The leg is involved. The contributor notes the lesion is raised or bumpy. Skin tone: Fitzpatrick phototype II. The patient described the issue as acne. Symptoms reported: bothersome appearance. The photo was captured at a distance. The contributor notes the condition has been present for three to twelve months.
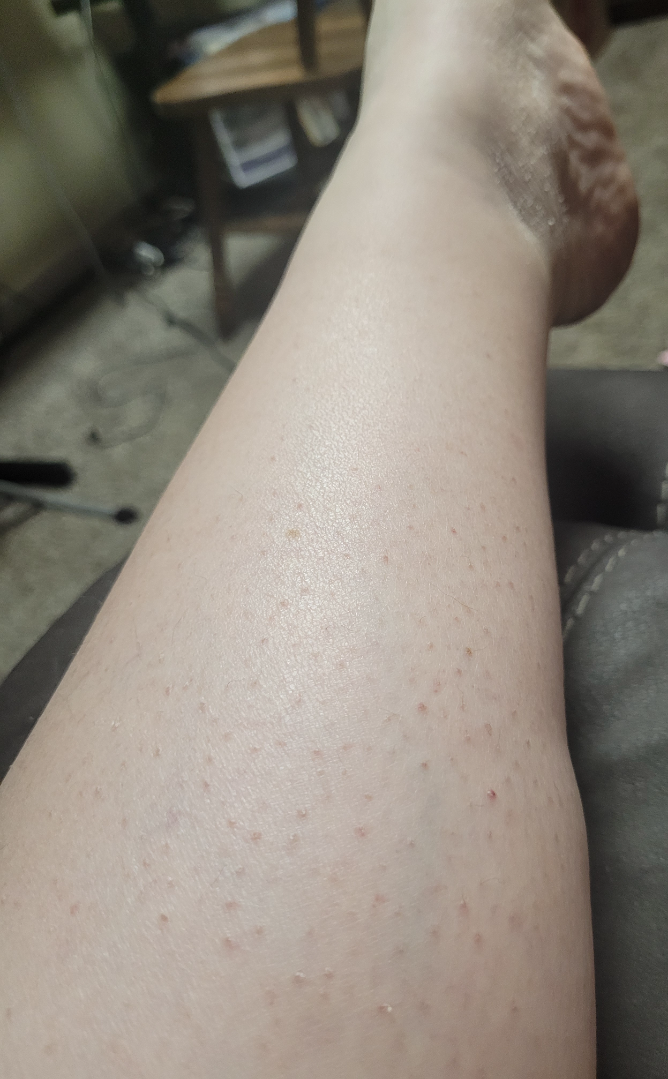The reviewing dermatologist's impression was: Keratosis pilaris (most likely); Folliculitis (considered).